A female subject aged 47; the patient is Fitzpatrick skin type II; a clinical photograph of a skin lesion; history notes alcohol use, prior malignancy (patient or family), and no tobacco use: 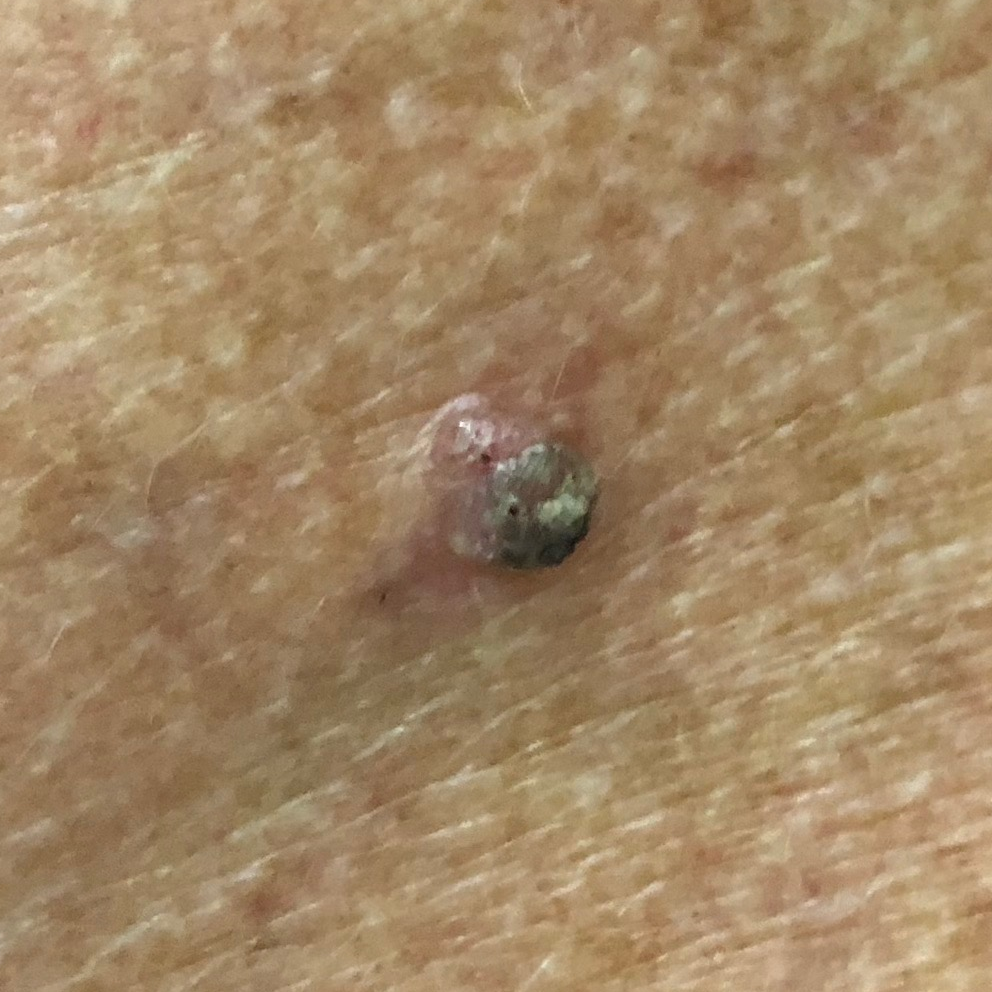The lesion is located on the chest. The lesion is roughly 7 by 5 mm. By the patient's account, the lesion is elevated. The biopsy diagnosis was a lesion of indeterminate malignant potential — an actinic keratosis.